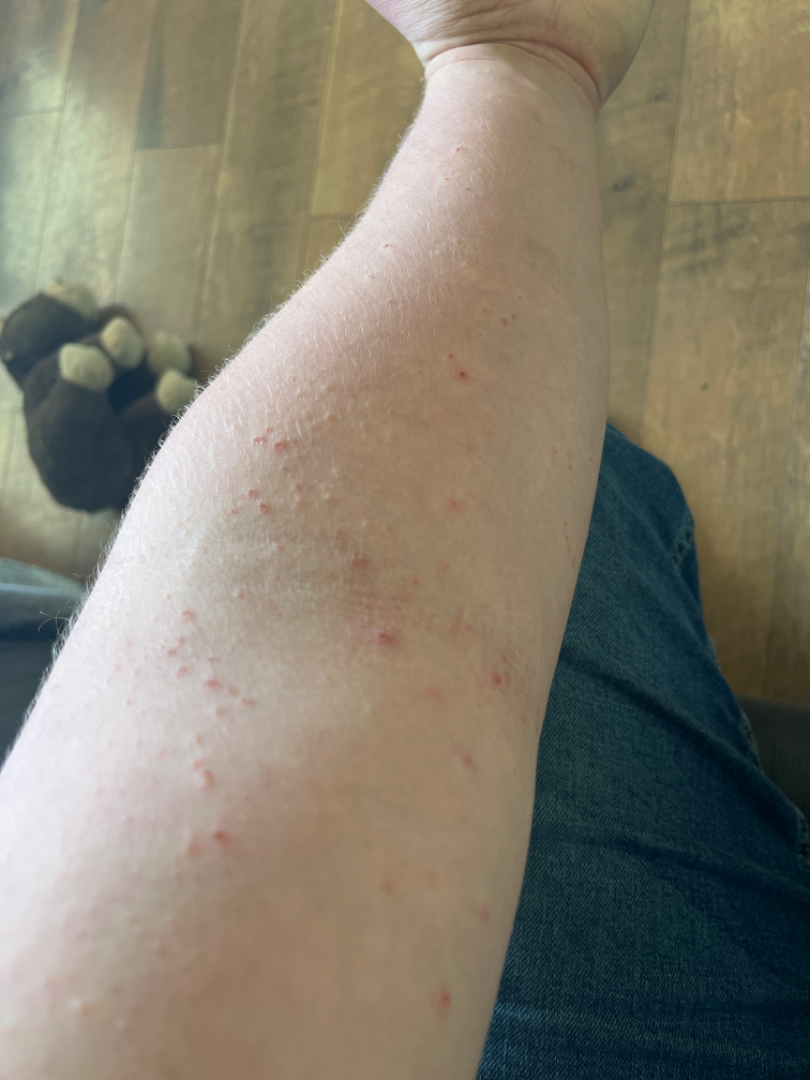A close-up photograph. The contributor is a male aged 18–29. The head or neck and arm are involved. On remote review of the image, the leading impression is Eczema.